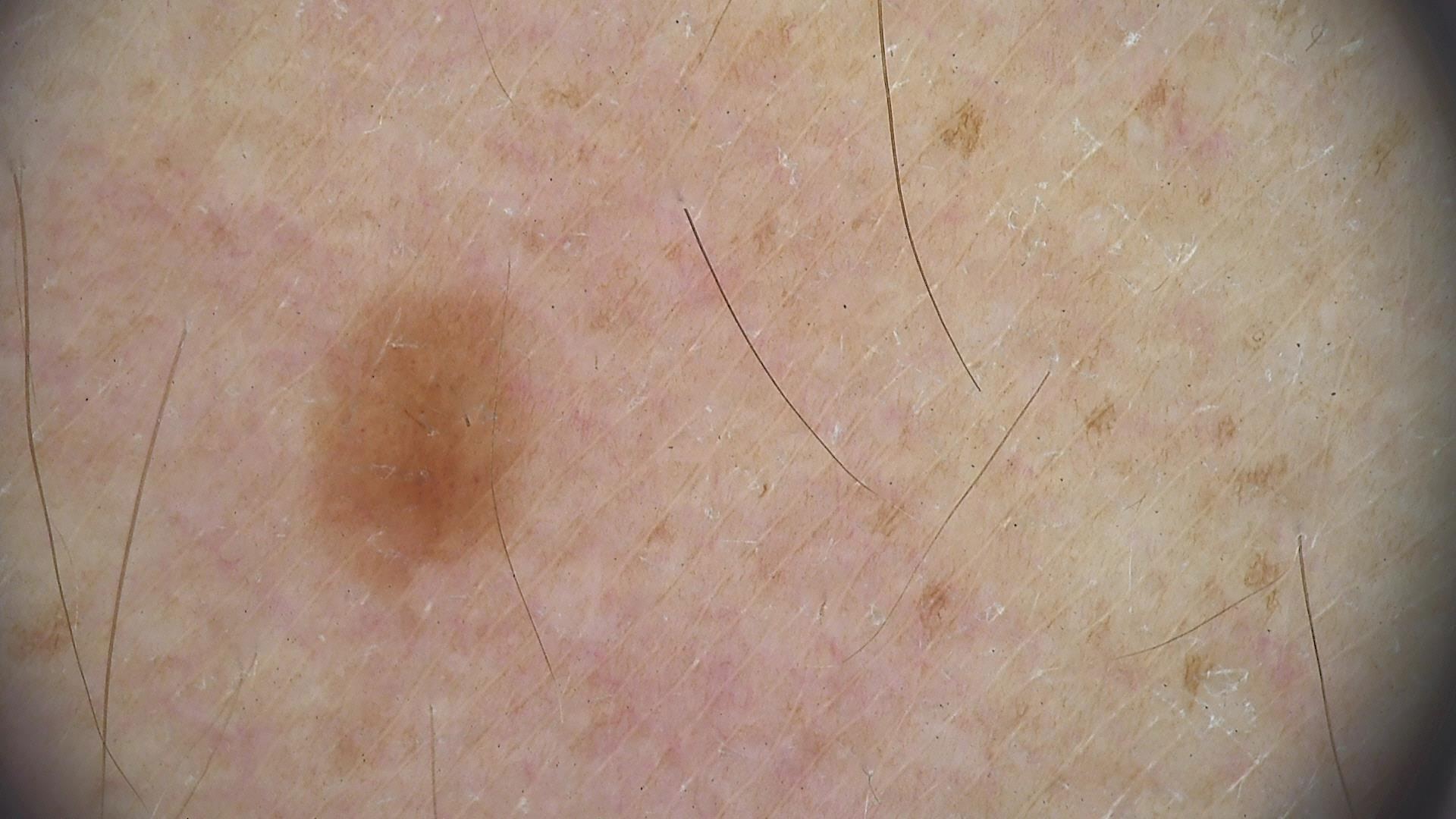  diagnosis:
    name: dysplastic junctional nevus
    code: jd
    malignancy: benign
    super_class: melanocytic
    confirmation: expert consensus